A clinical photograph of a skin lesion; a male subject age 50; the patient is skin type II; history notes pesticide exposure, prior malignancy (patient or family), tobacco use, and alcohol use.
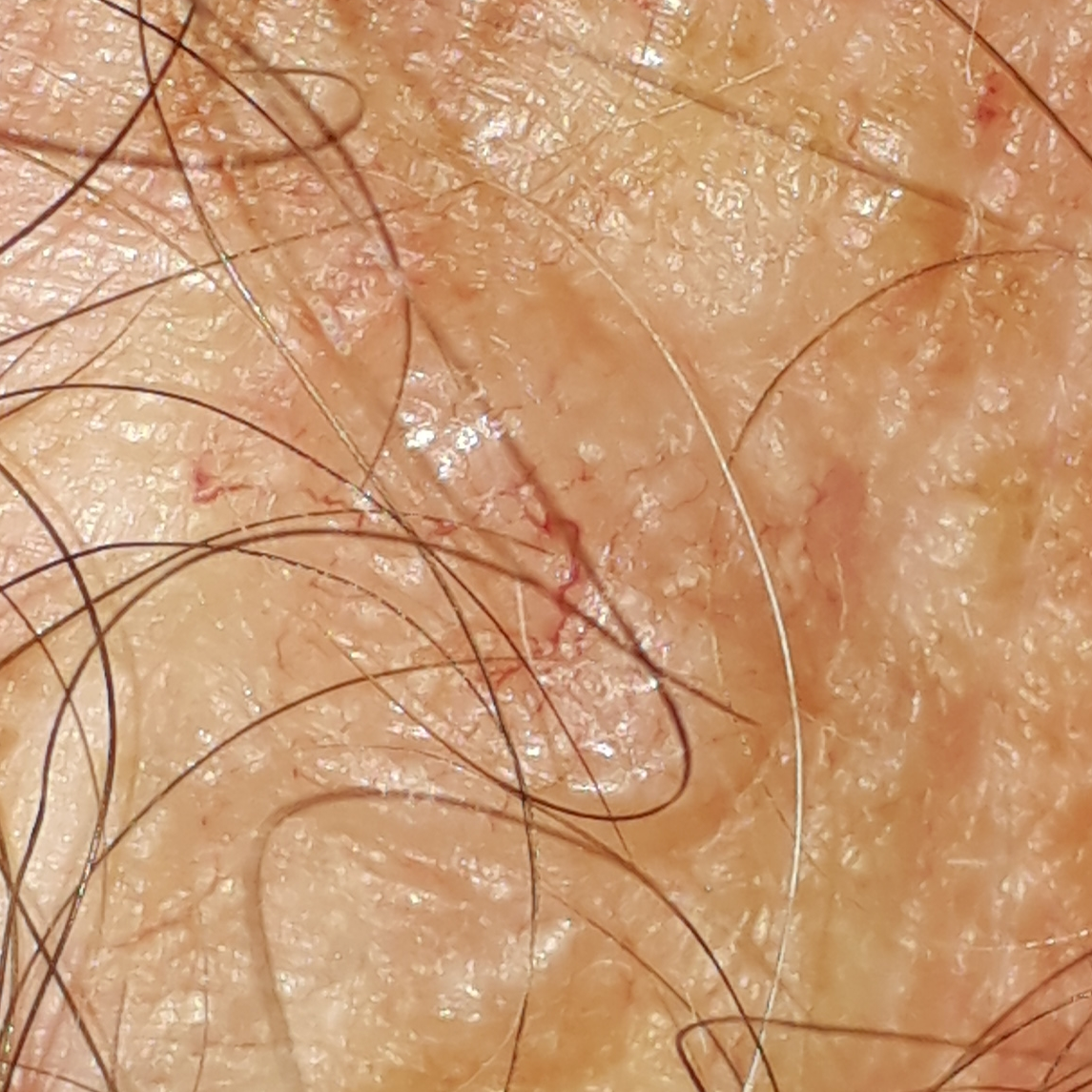Case summary: The lesion is on the chest. The lesion is roughly 16 by 10 mm. By the patient's account, the lesion has grown and is elevated. Diagnosis: Histopathology confirmed a basal cell carcinoma.